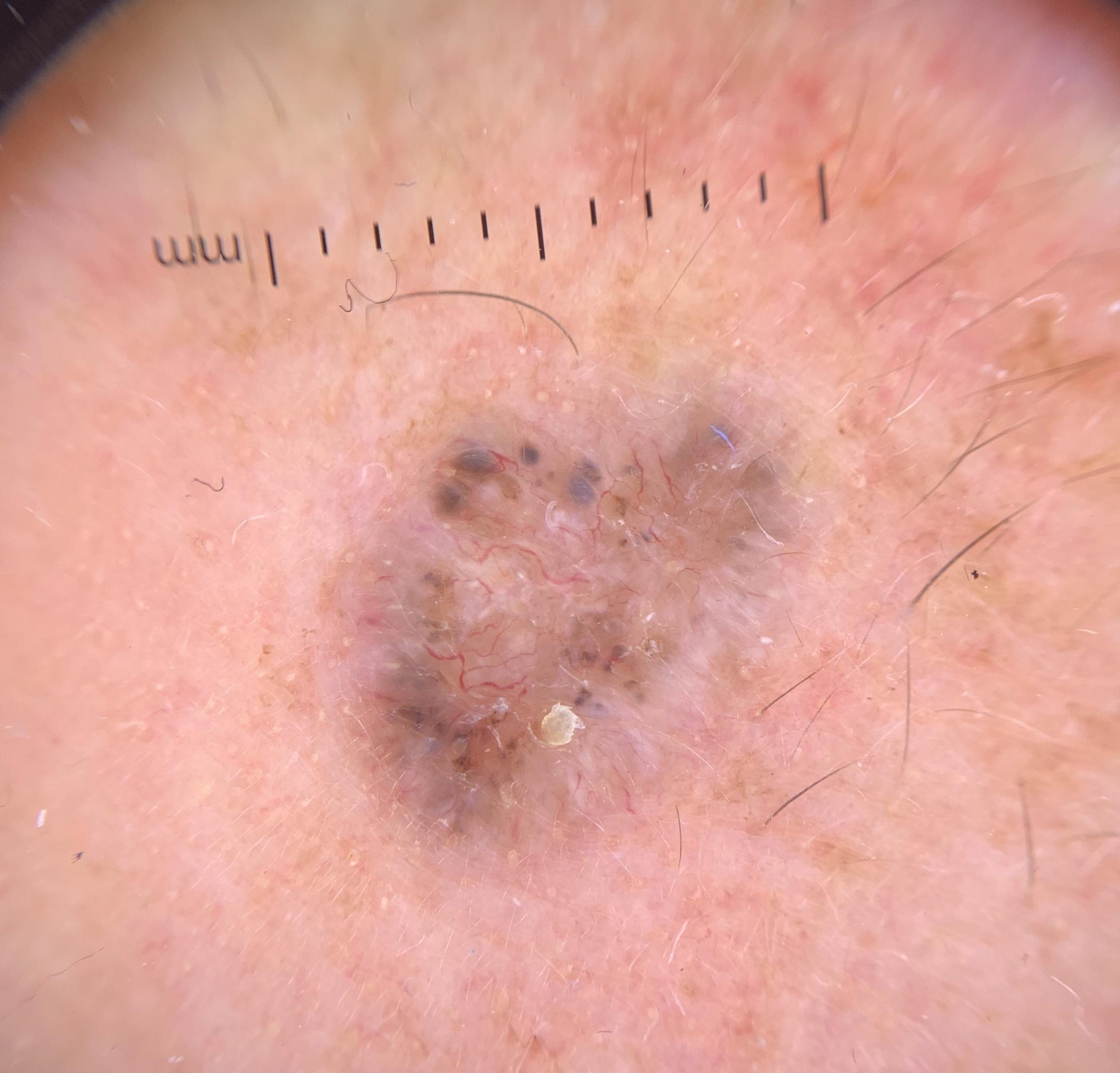Q: Patient demographics?
A: female, aged around 80
Q: What is the patient's skin type?
A: II
Q: What is the imaging modality?
A: contact-polarized dermoscopy
Q: What is the anatomic site?
A: the head or neck
Q: What did the workup show?
A: Basal cell carcinoma (biopsy-proven)